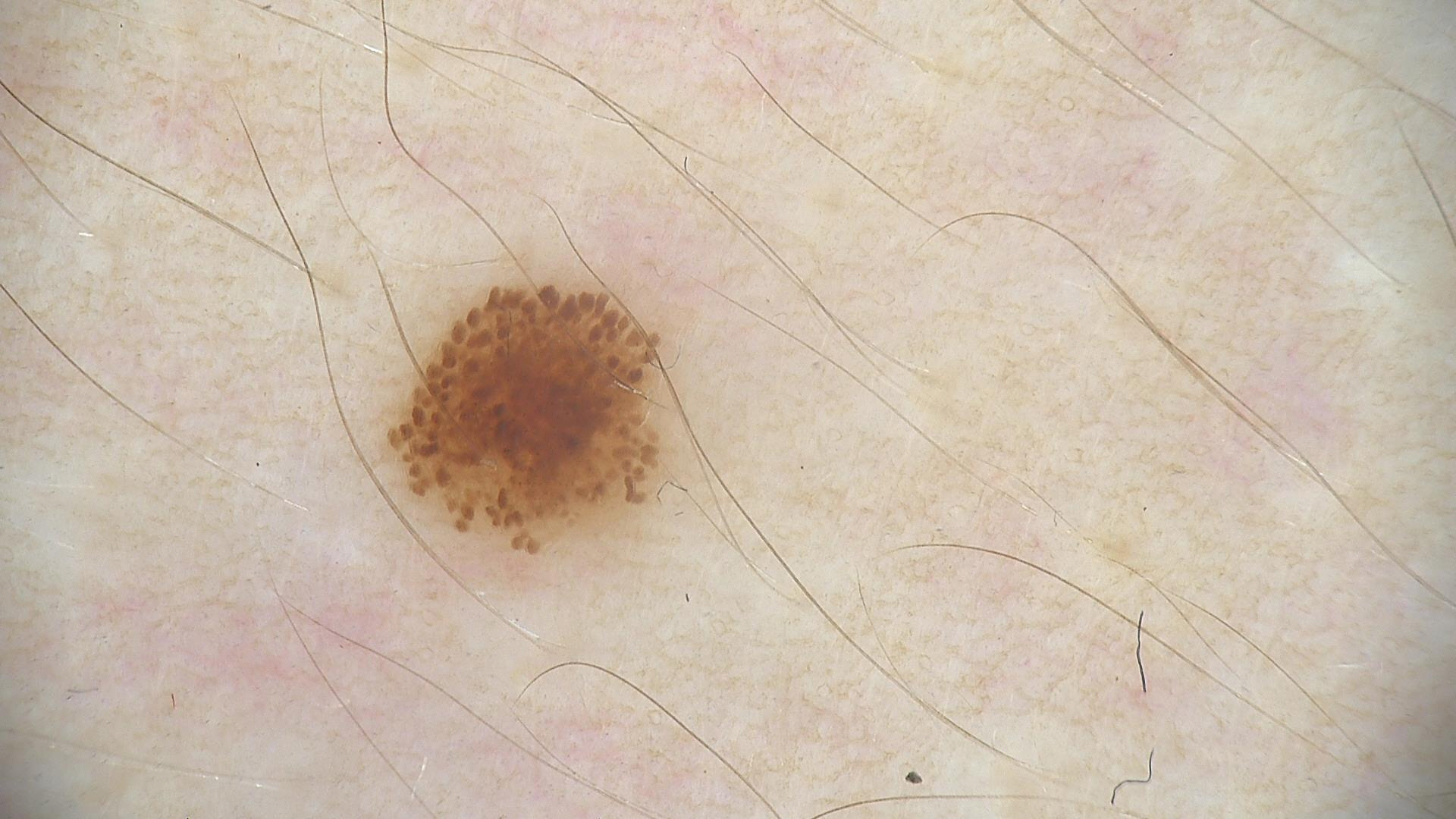A skin lesion imaged with a dermatoscope. The morphology is that of a banal lesion. Consistent with a compound nevus.